A clinical close-up photograph of a skin lesion; history notes prior malignancy (patient or family) and pesticide exposure; a male subject age 71 — 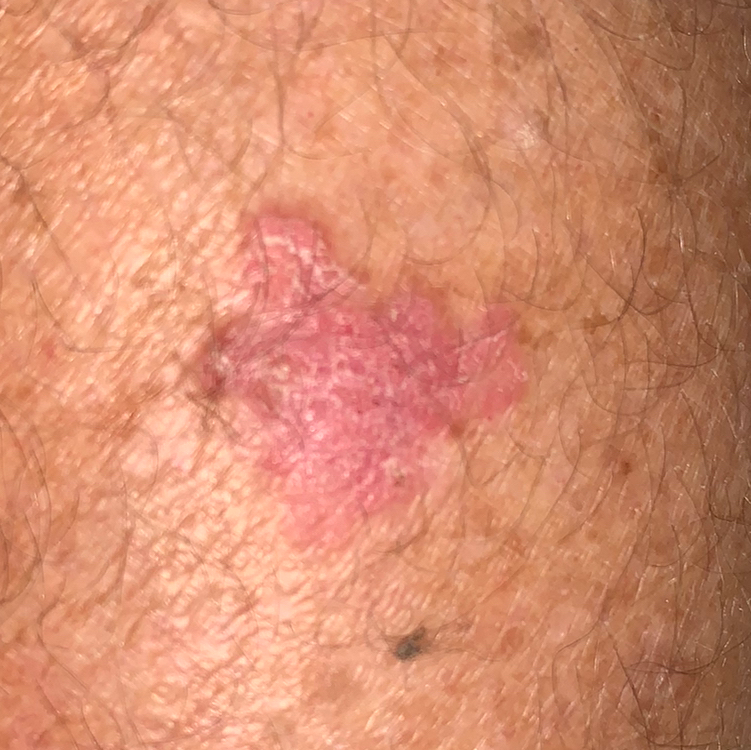Patient and lesion: The lesion is located on a thigh. By the patient's account, the lesion is elevated and itches. Diagnosis: Histopathological examination showed an actinic keratosis.